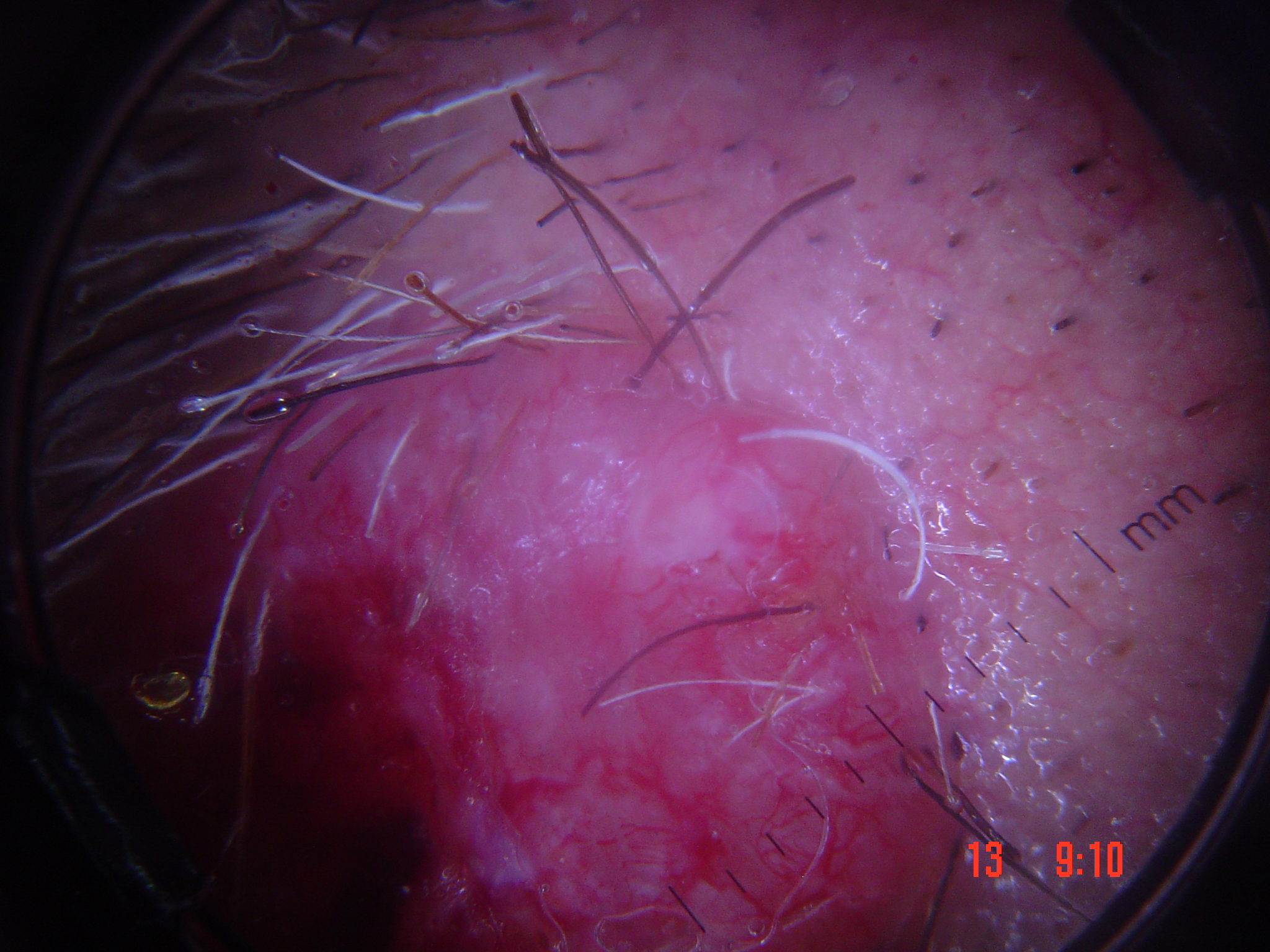Histopathologically confirmed as a keratinocytic lesion — a squamous cell carcinoma.